A dermoscopic close-up of a skin lesion:
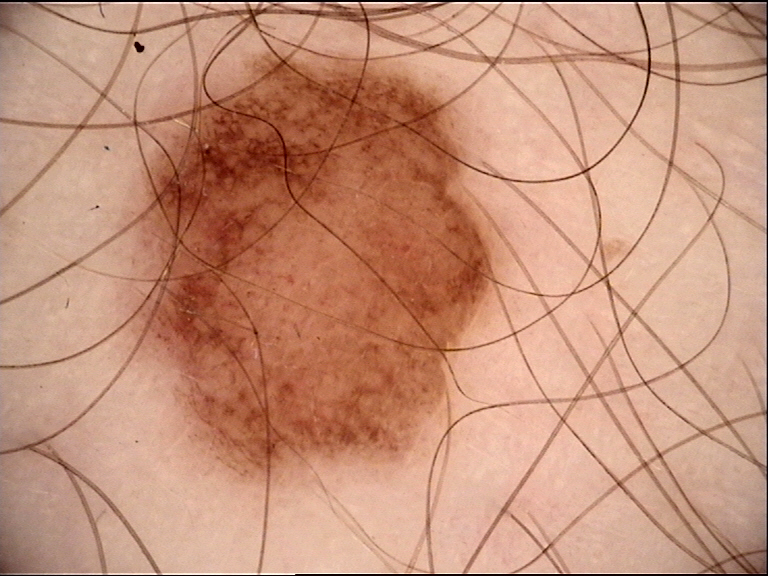The morphology is that of a banal lesion.
The diagnosis was a compound nevus.